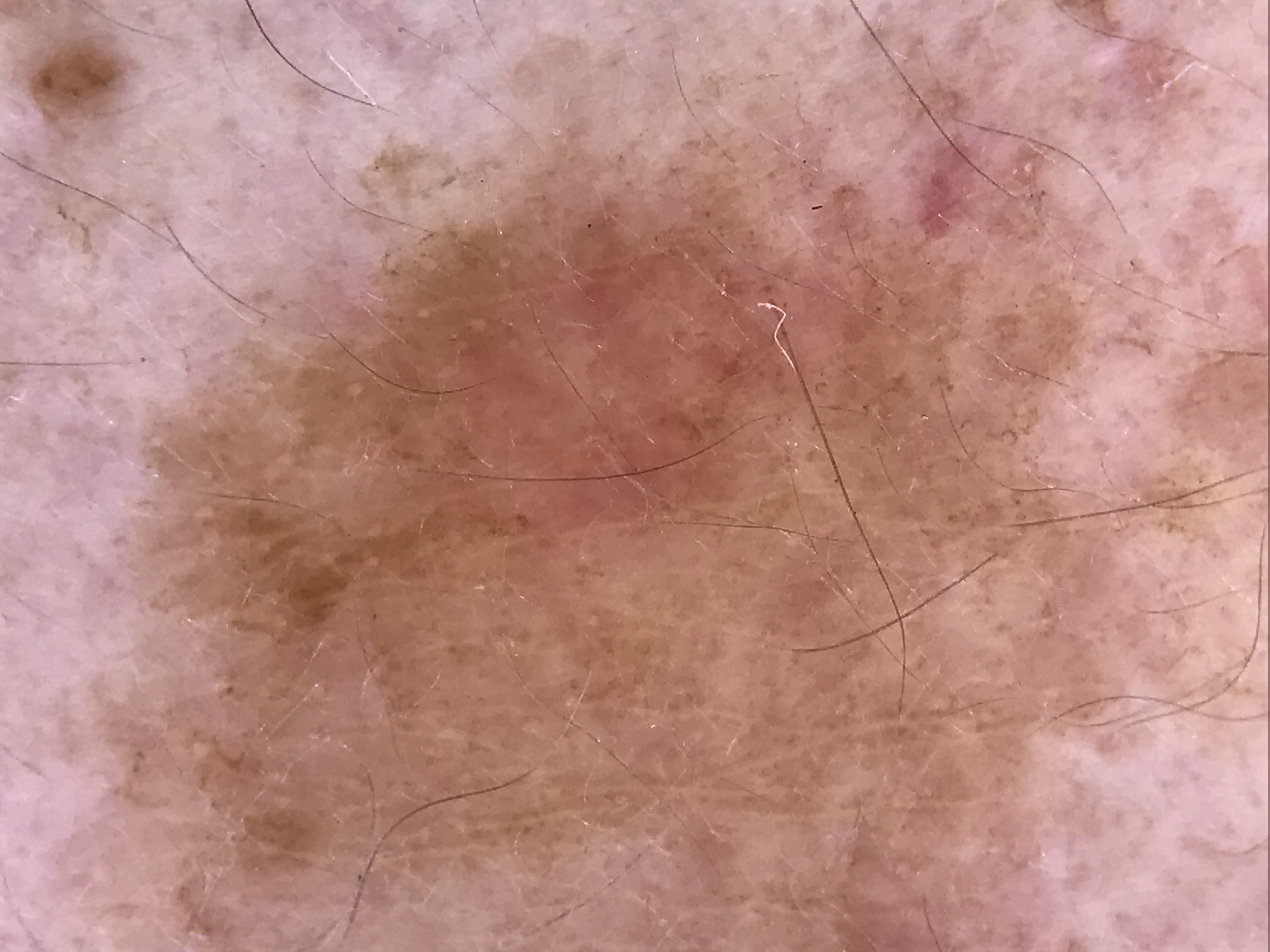<dermoscopy>
<diagnosis>
<name>solar lentigo</name>
<code>sl</code>
<malignancy>benign</malignancy>
<super_class>melanocytic</super_class>
<confirmation>expert consensus</confirmation>
</diagnosis>
</dermoscopy>